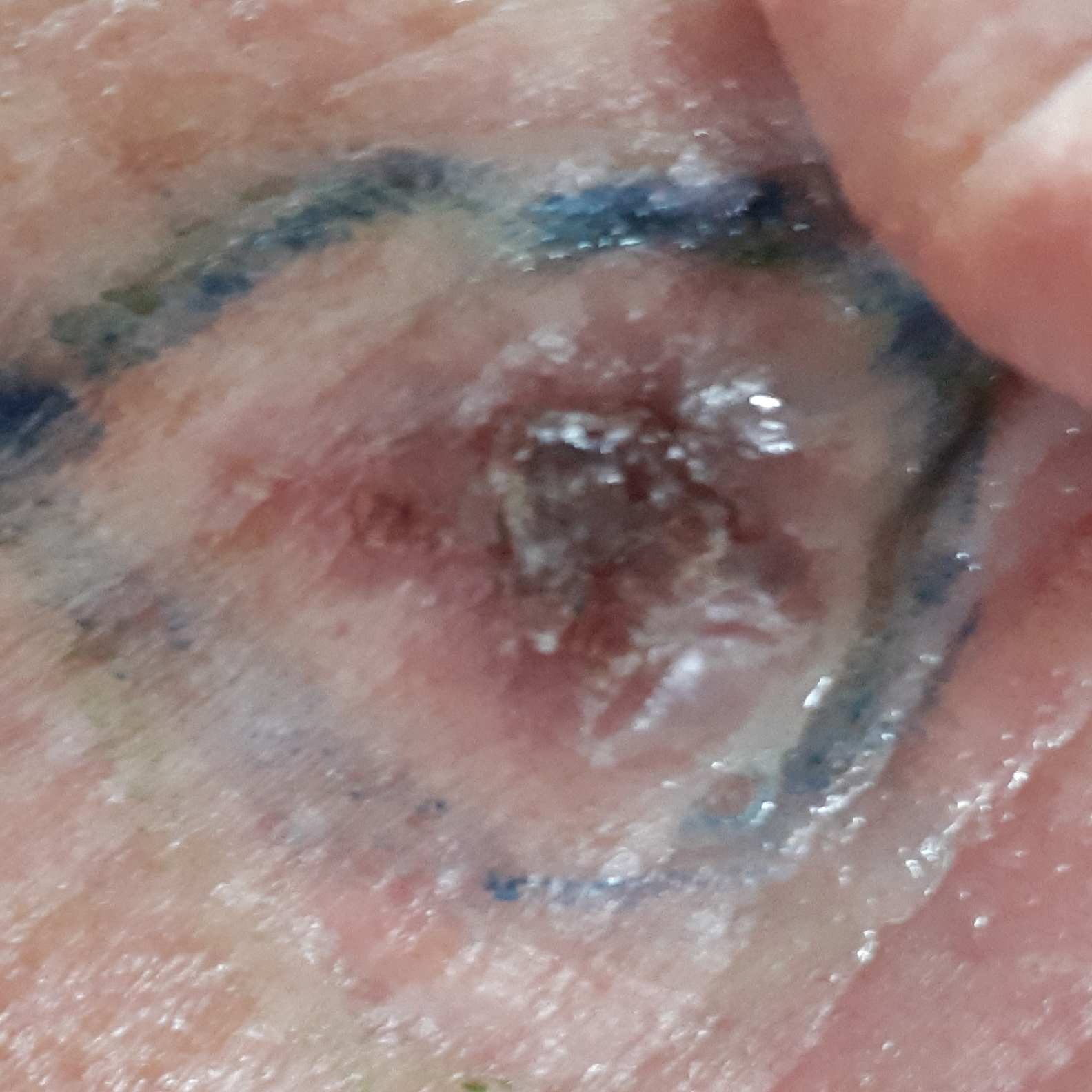By history, prior skin cancer (patient or family), tobacco use, and pesticide exposure. The patient was assessed as Fitzpatrick skin type II. The lesion involves the face. The lesion is roughly 13 by 10 mm. Per patient report, the lesion is elevated, hurts, has bled, and itches. Histopathologically confirmed as a basal cell carcinoma.